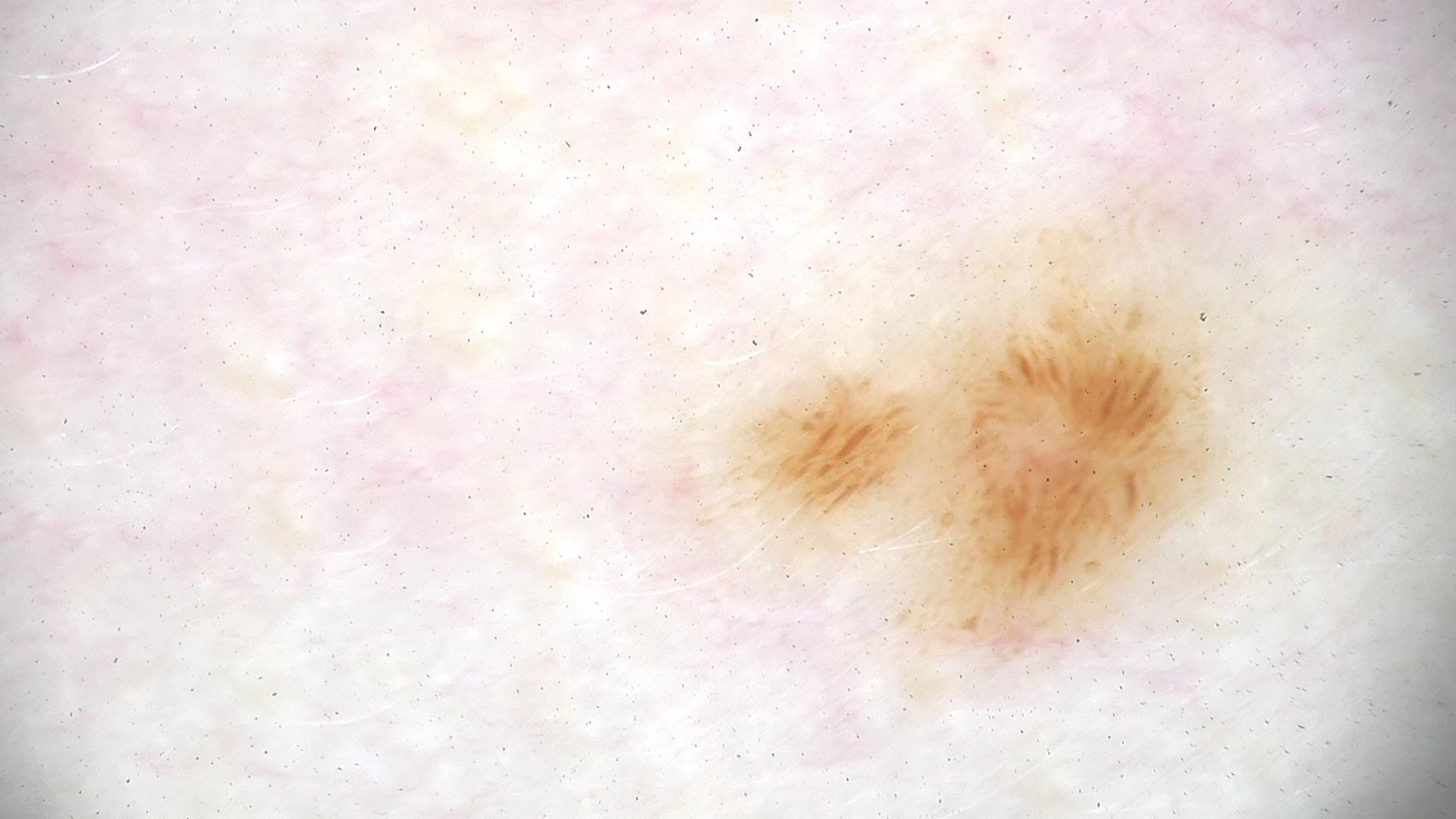Q: What is the imaging modality?
A: dermatoscopy
Q: What is the diagnosis?
A: dysplastic junctional nevus (expert consensus)